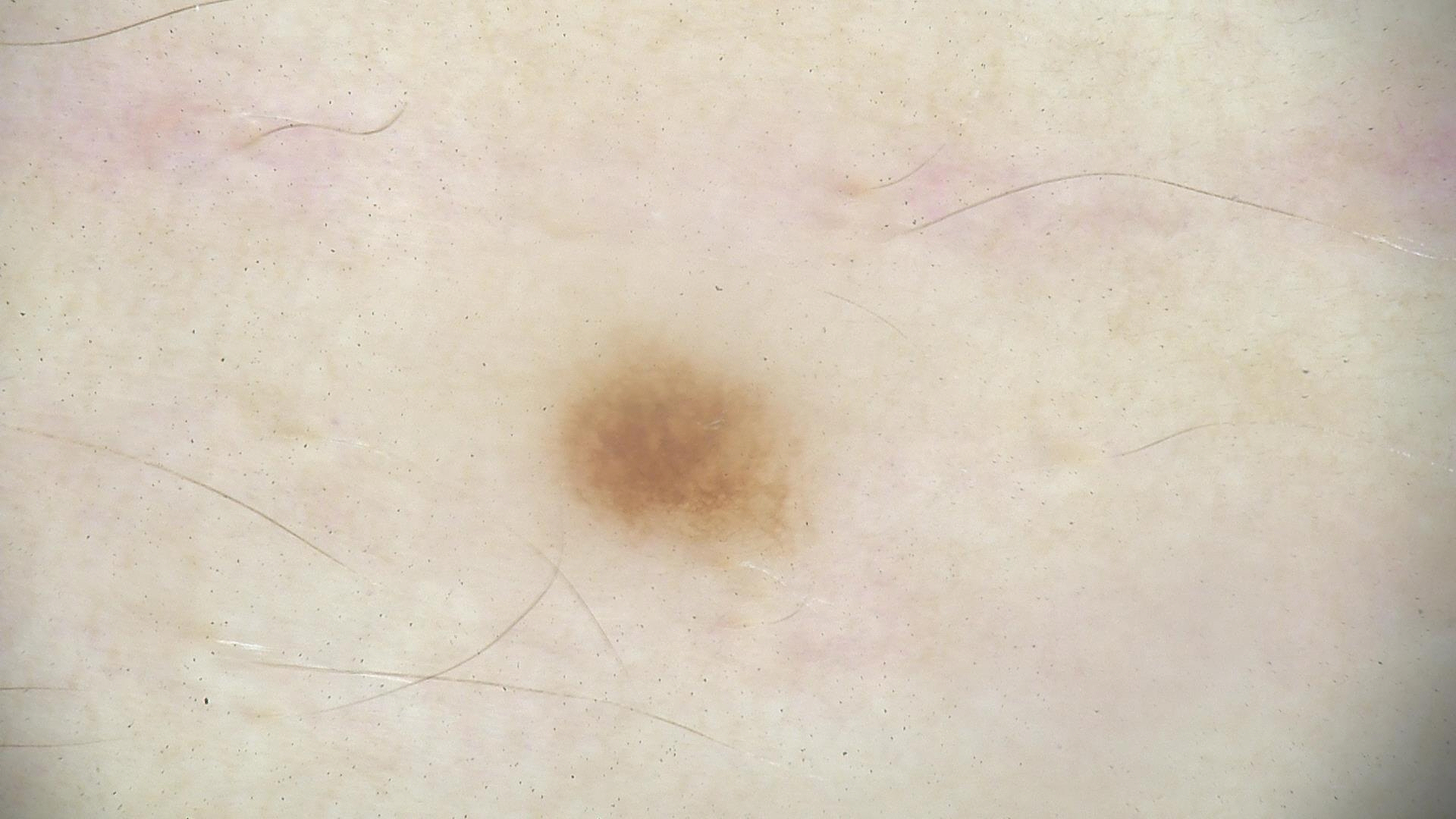image type — dermatoscopy; class — dysplastic junctional nevus (expert consensus).